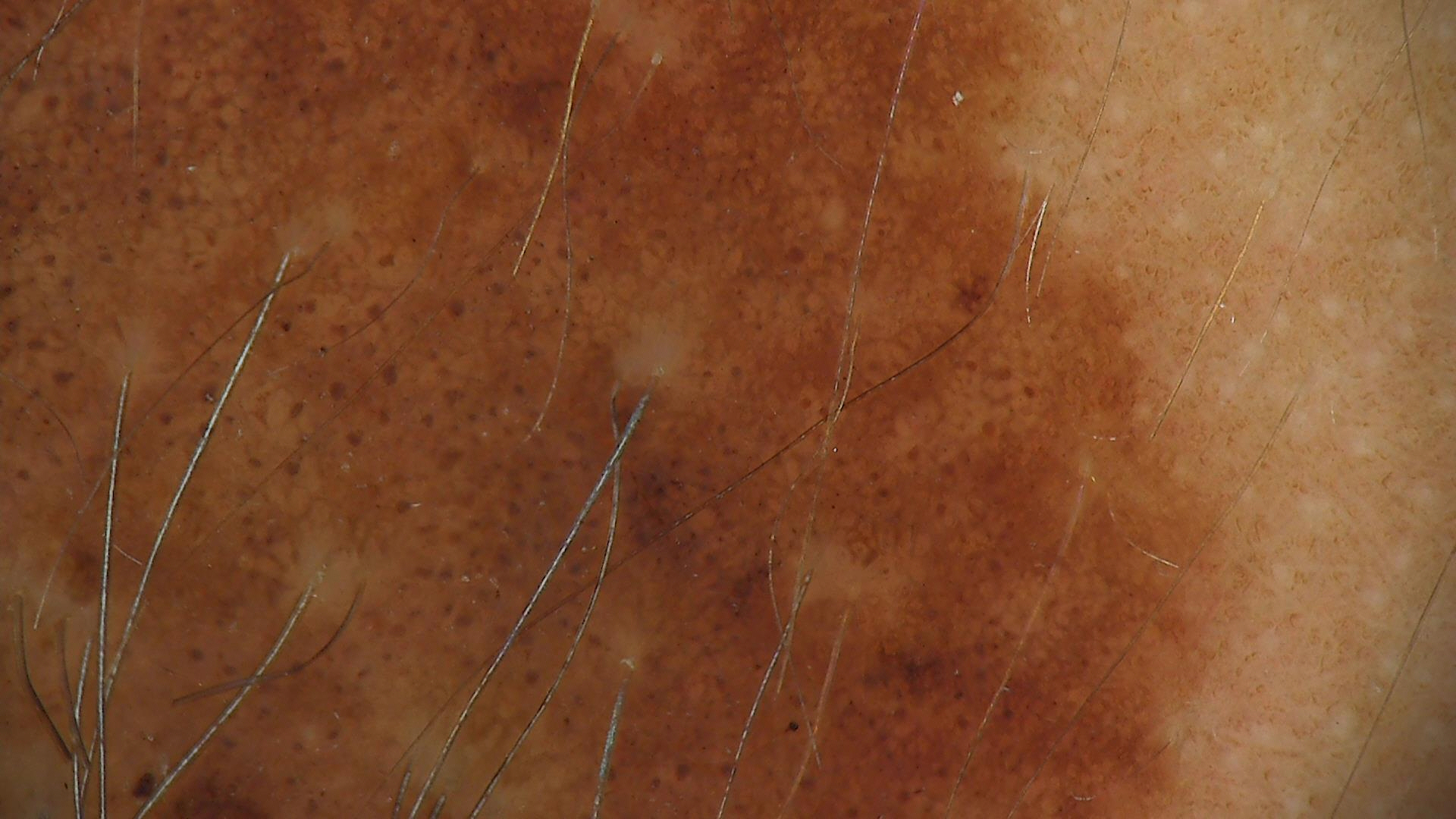Classified as a congenital junctional nevus.